The patient considered this a rash · located on the arm · the lesion is associated with itching, enlargement, burning and bothersome appearance · the contributor notes the lesion is rough or flaky and raised or bumpy · the photograph is a close-up of the affected area:
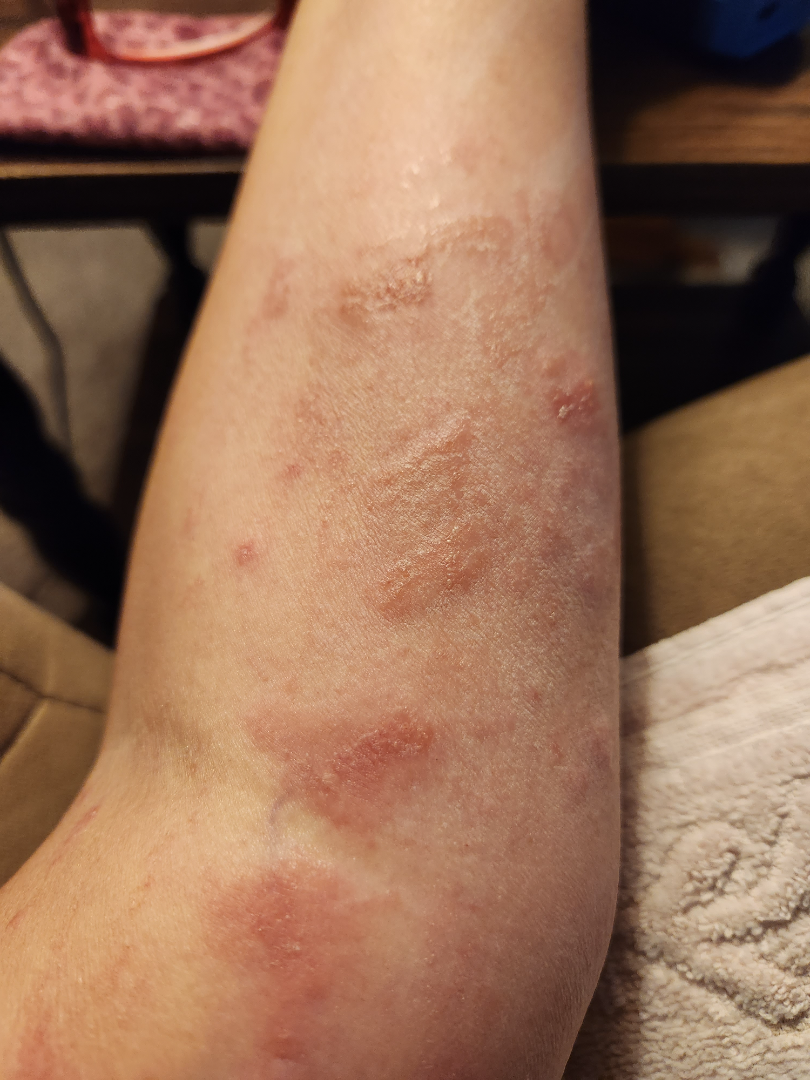{"differential": {"leading": ["Contact dermatitis"]}}